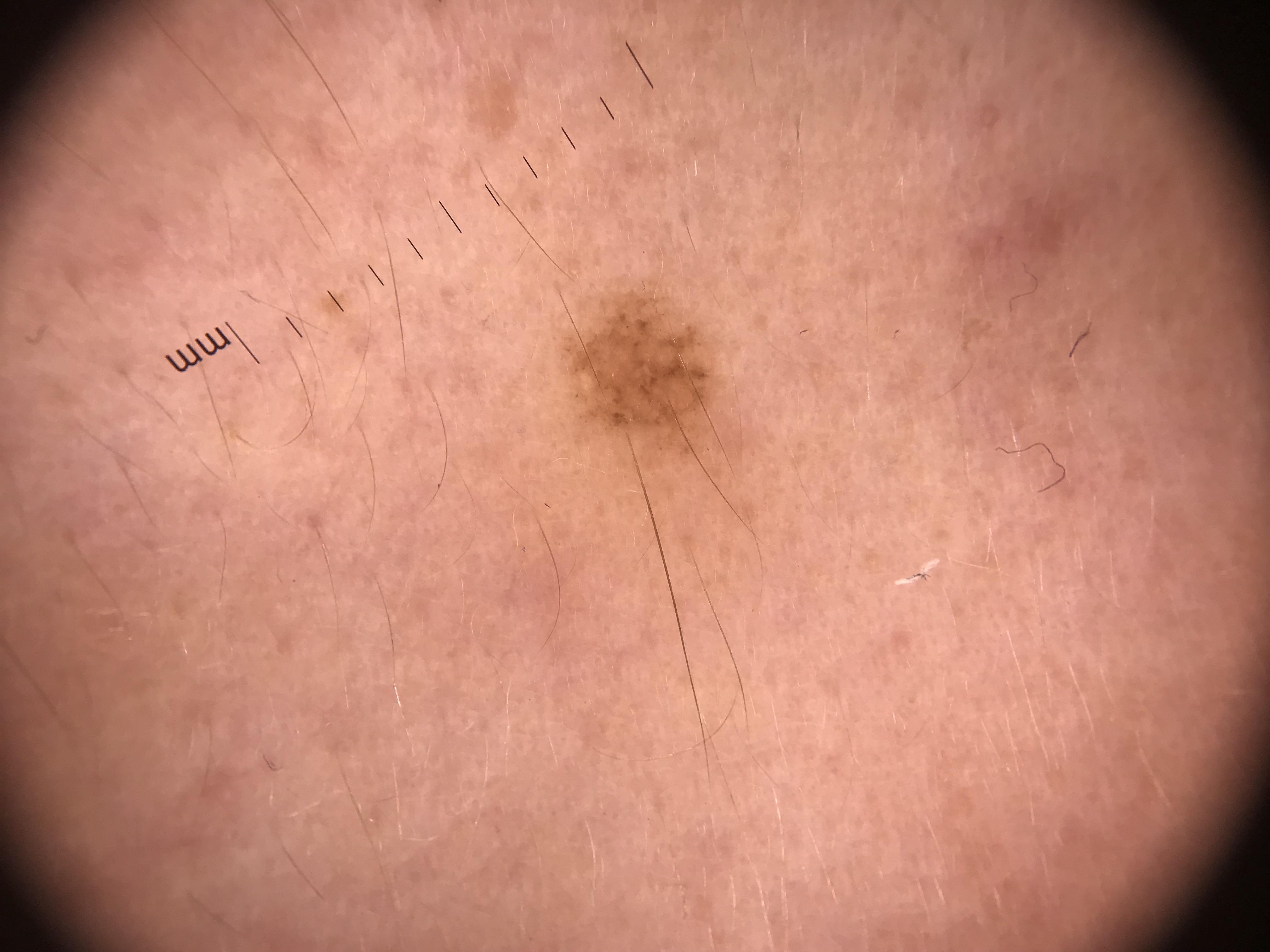class=Miescher nevus (expert consensus).